A male patient aged 89; the patient says their skin reddens painfully with sun exposure; acquired for a research image collection, with no referral diagnosis; a macroscopic clinical photograph of a skin lesion.
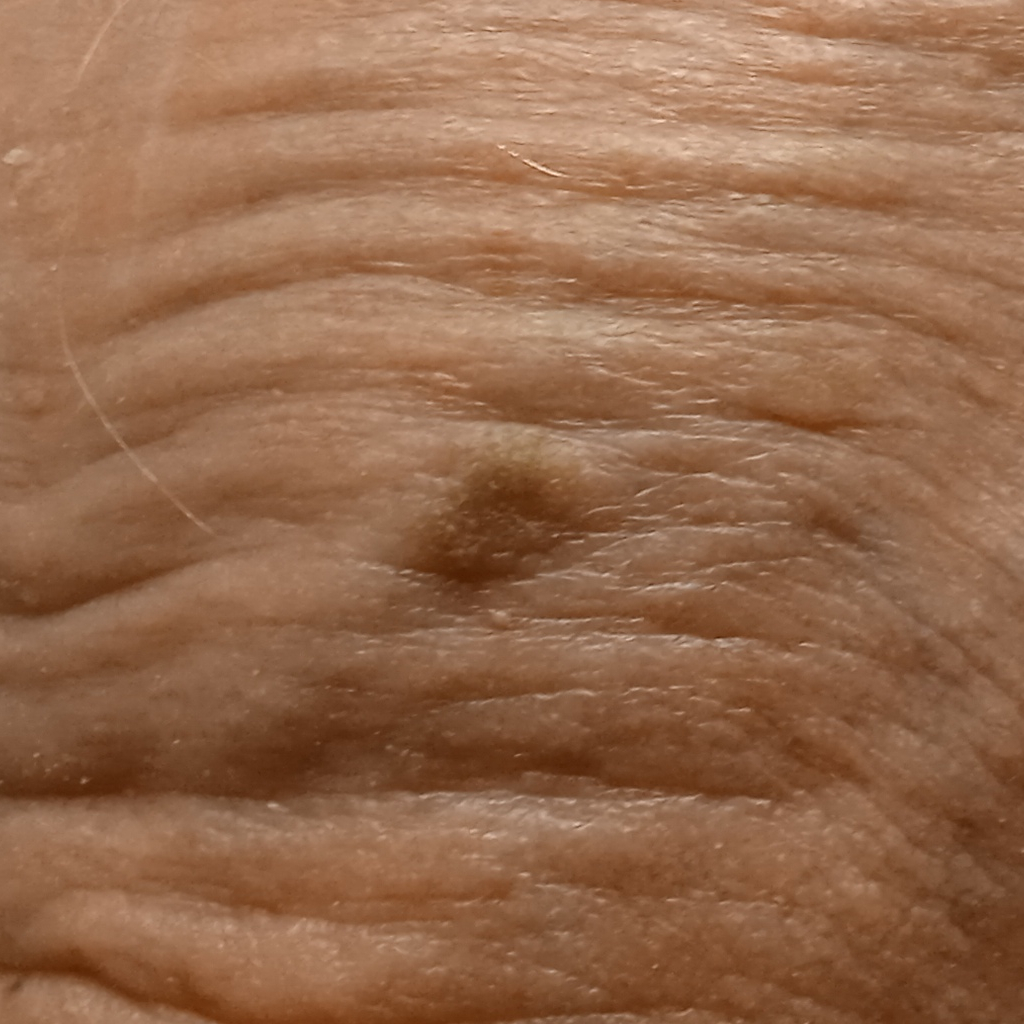The lesion involves the face. The lesion is about 6.4 mm across. The lesion was assessed as an actinic keratosis.